The patient says their skin reddens painfully with sun exposure · a female patient 50 years old · collected as part of a research study, without a referral diagnosis · the patient describes having a moderate number of moles · a dermoscopic image of a skin lesion.
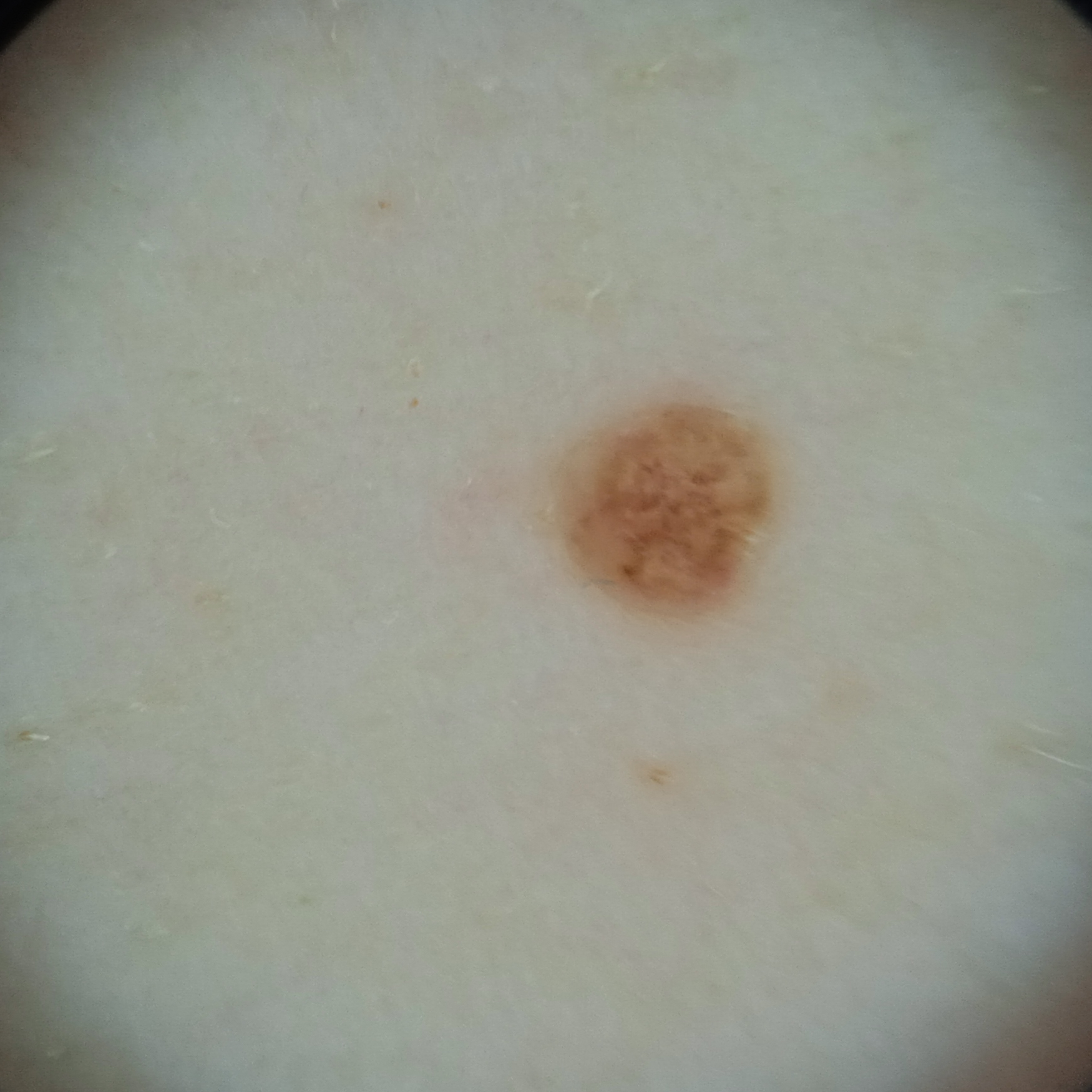<record>
  <lesion_location>the back</lesion_location>
  <lesion_size>
    <diameter_mm>2.2</diameter_mm>
  </lesion_size>
  <diagnosis>
    <name>melanocytic nevus</name>
    <malignancy>benign</malignancy>
  </diagnosis>
</record>